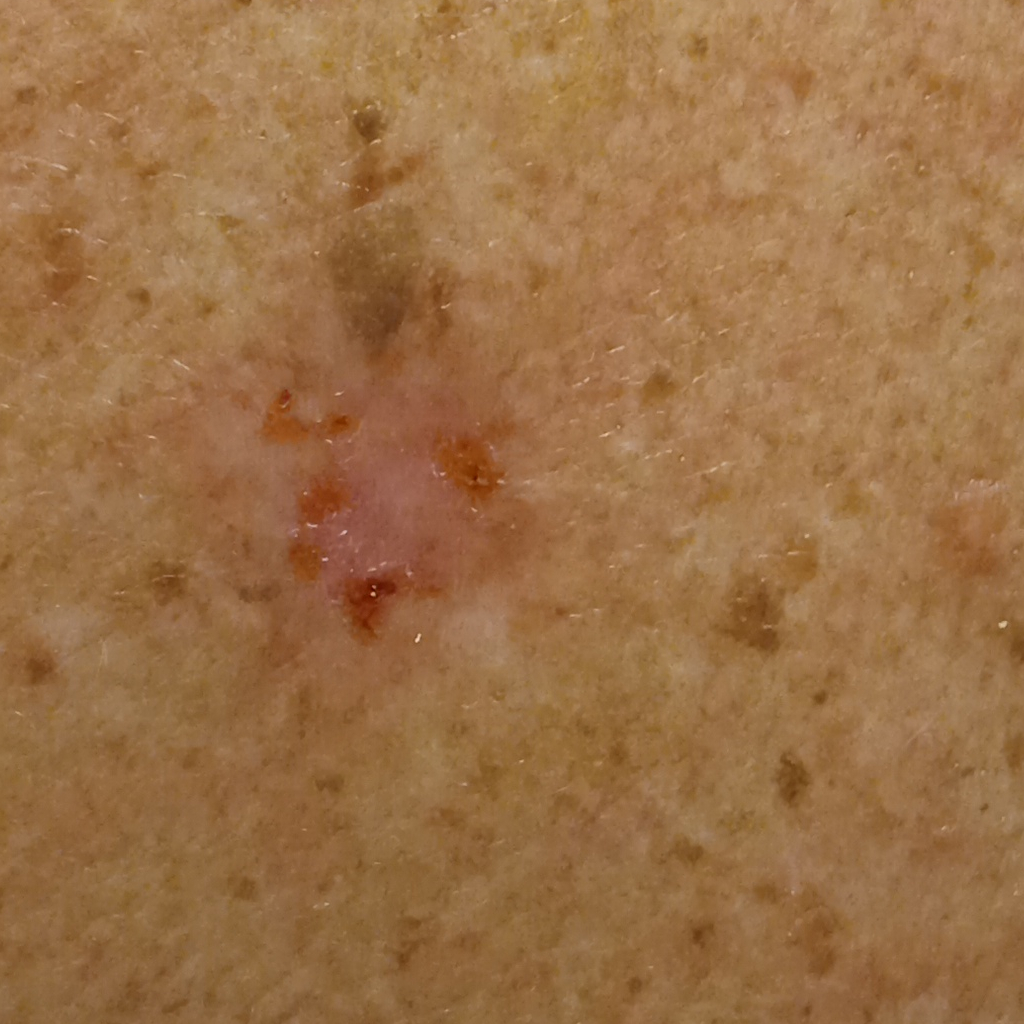A male patient aged 81. Few moles overall by the patient's own estimate. The referring clinician suspected basal cell carcinoma. On a questionnaire the patient reported a personal history of cancer and a family history of skin cancer. The lesion is on the back. Histopathology confirmed a basal cell carcinoma, following excision, with tumor thickness 3 mm.